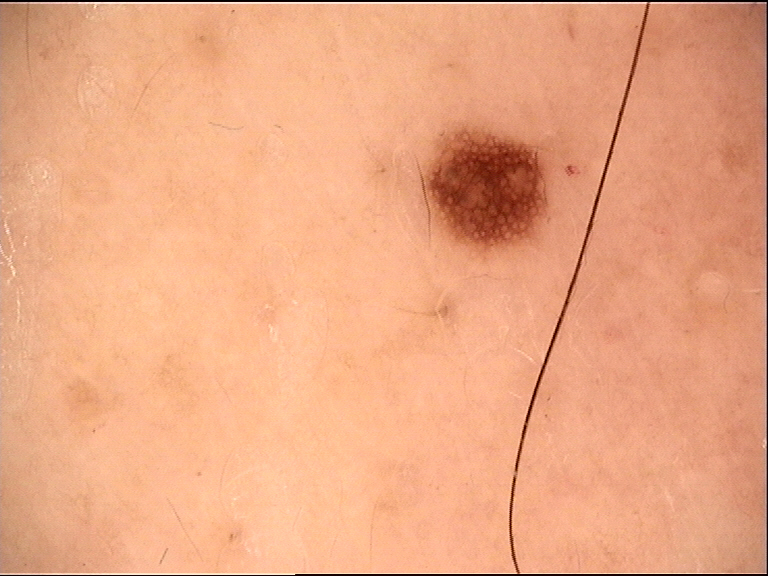<lesion>
  <image>dermoscopy</image>
  <diagnosis>
    <name>dysplastic junctional nevus</name>
    <code>jd</code>
    <malignancy>benign</malignancy>
    <super_class>melanocytic</super_class>
    <confirmation>expert consensus</confirmation>
  </diagnosis>
</lesion>